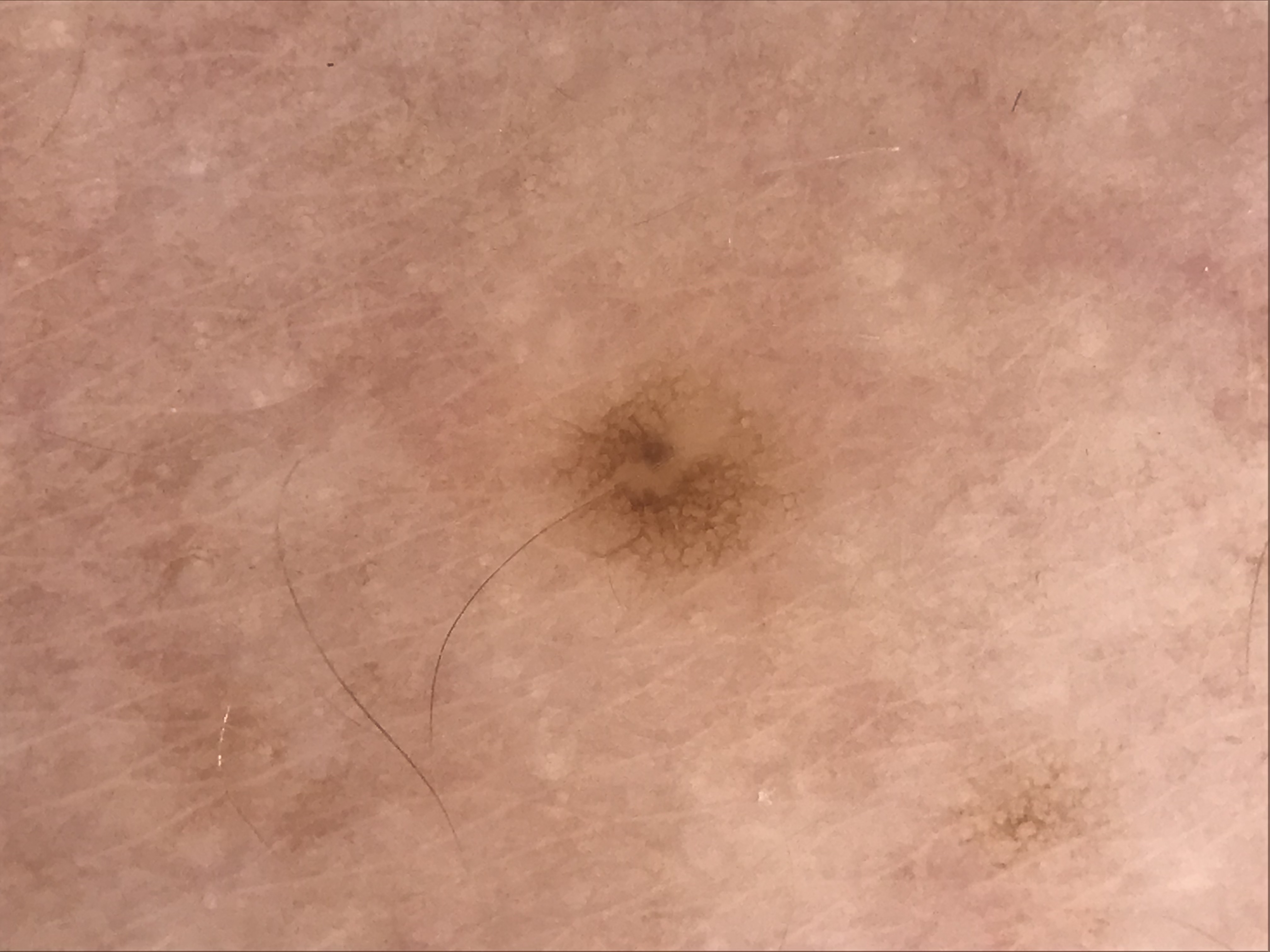Case:
A dermoscopy image of a single skin lesion. The architecture is that of a banal lesion.
Conclusion:
Classified as a junctional nevus.